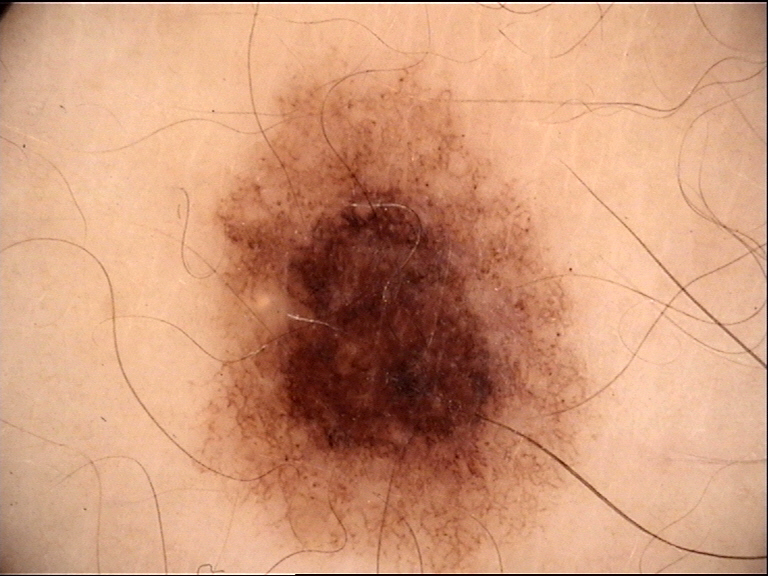label=dysplastic junctional nevus (expert consensus)